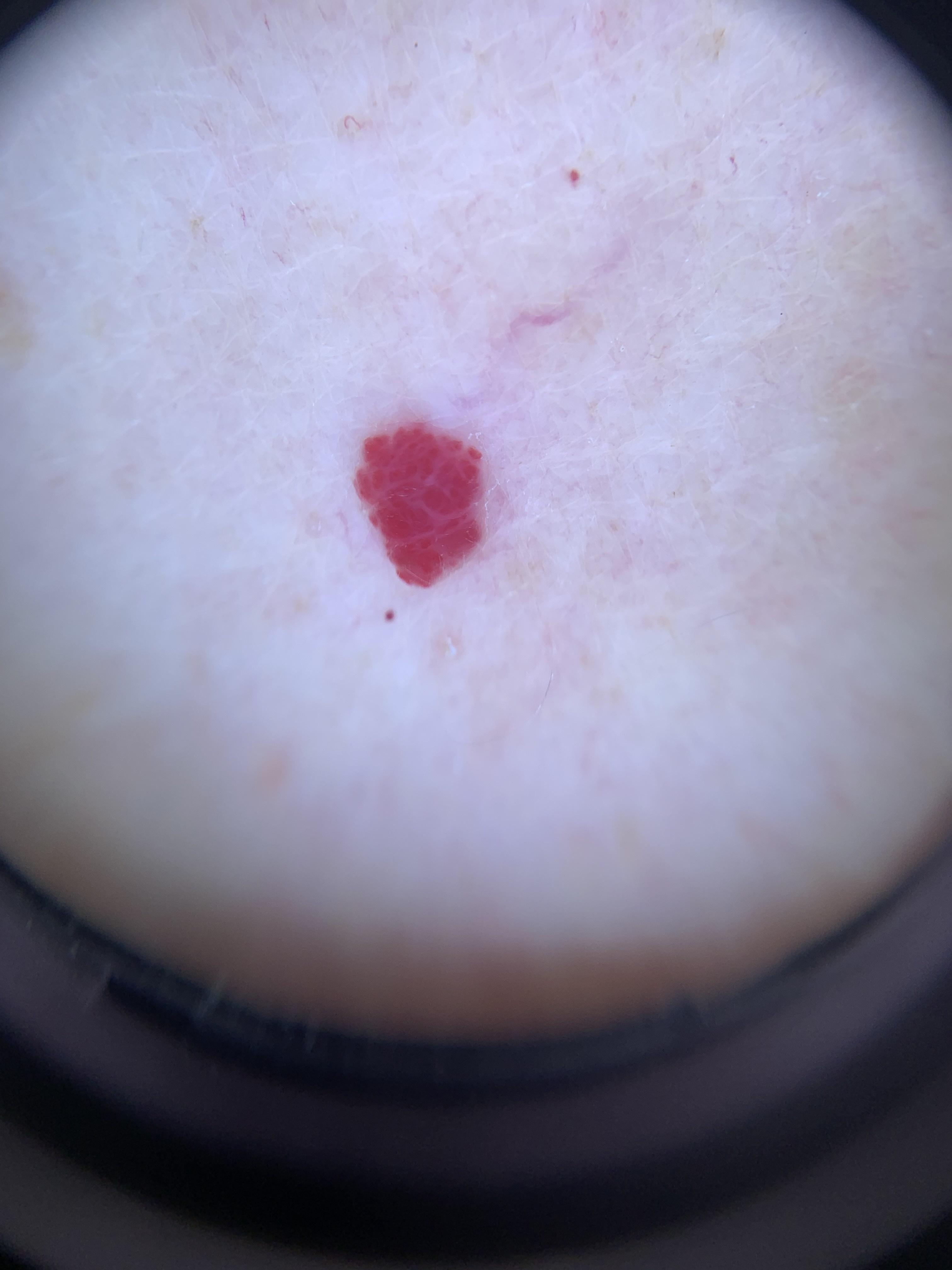Contact-polarized dermoscopy of a skin lesion.
Recorded as skin type II.
The lesion was found on an upper extremity.
Expert review favored a benign vascular lesion.